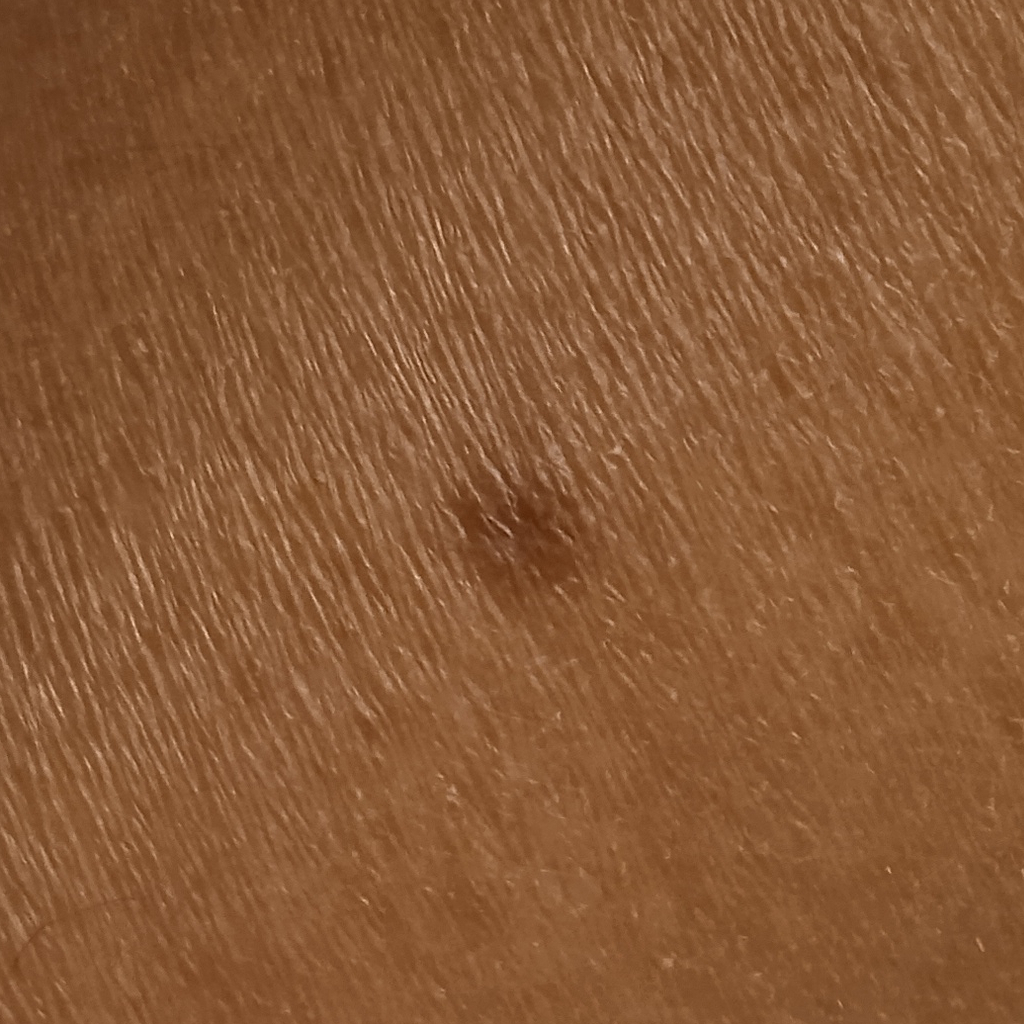• patient: female, age 58
• referral: research study (no referral diagnosis)
• nevus count: a moderate number of melanocytic nevi
• sun reaction: skin tans without first burning
• site: a leg
• diameter: 5.2 mm
• diagnosis: dermatofibroma (dermatologist consensus)